A skin lesion imaged with a dermatoscope:
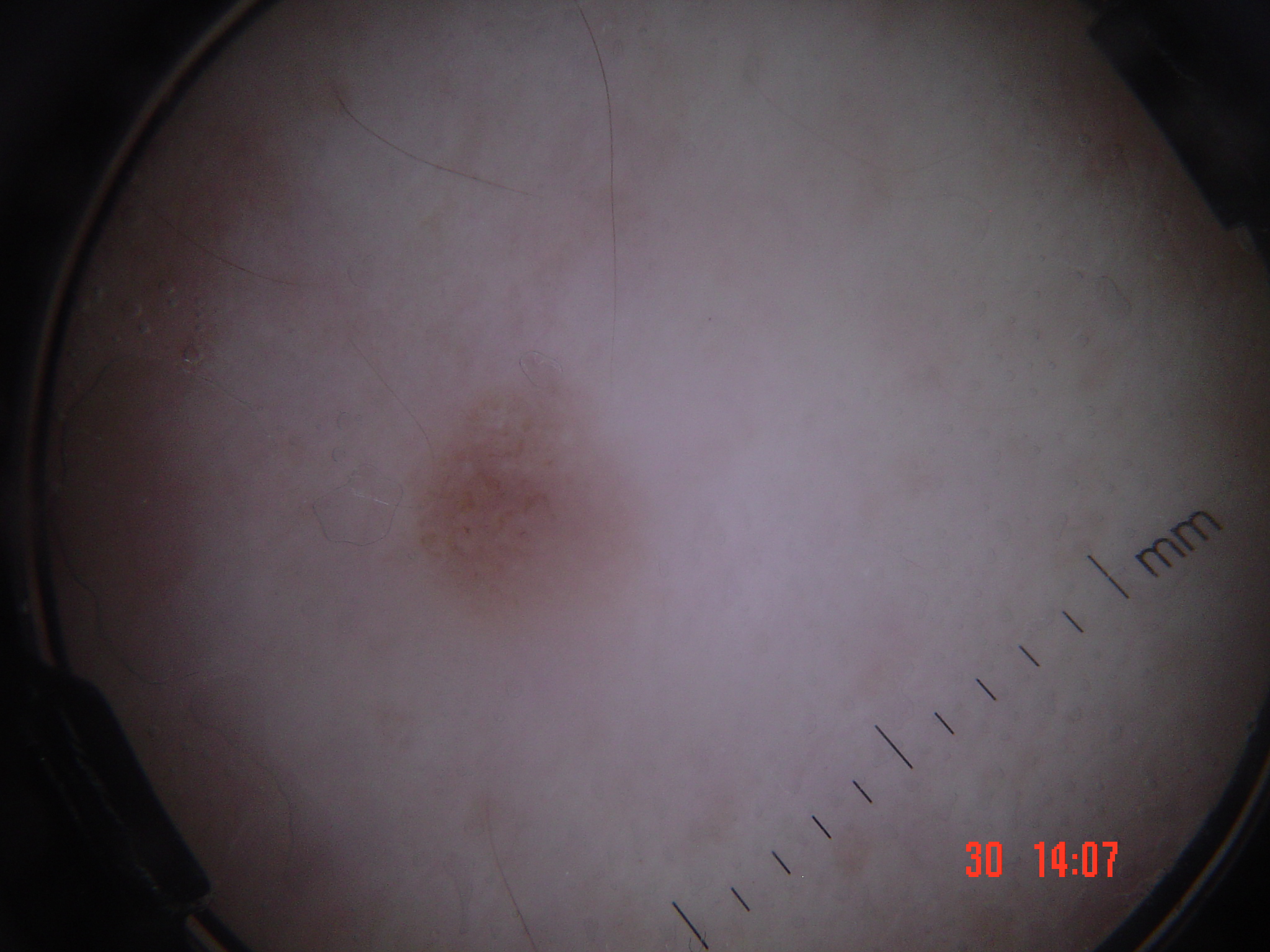category = keratinocytic | assessment = seborrheic keratosis (expert consensus).